A female patient, about 75 years old · this is a dermoscopic photograph of a skin lesion: 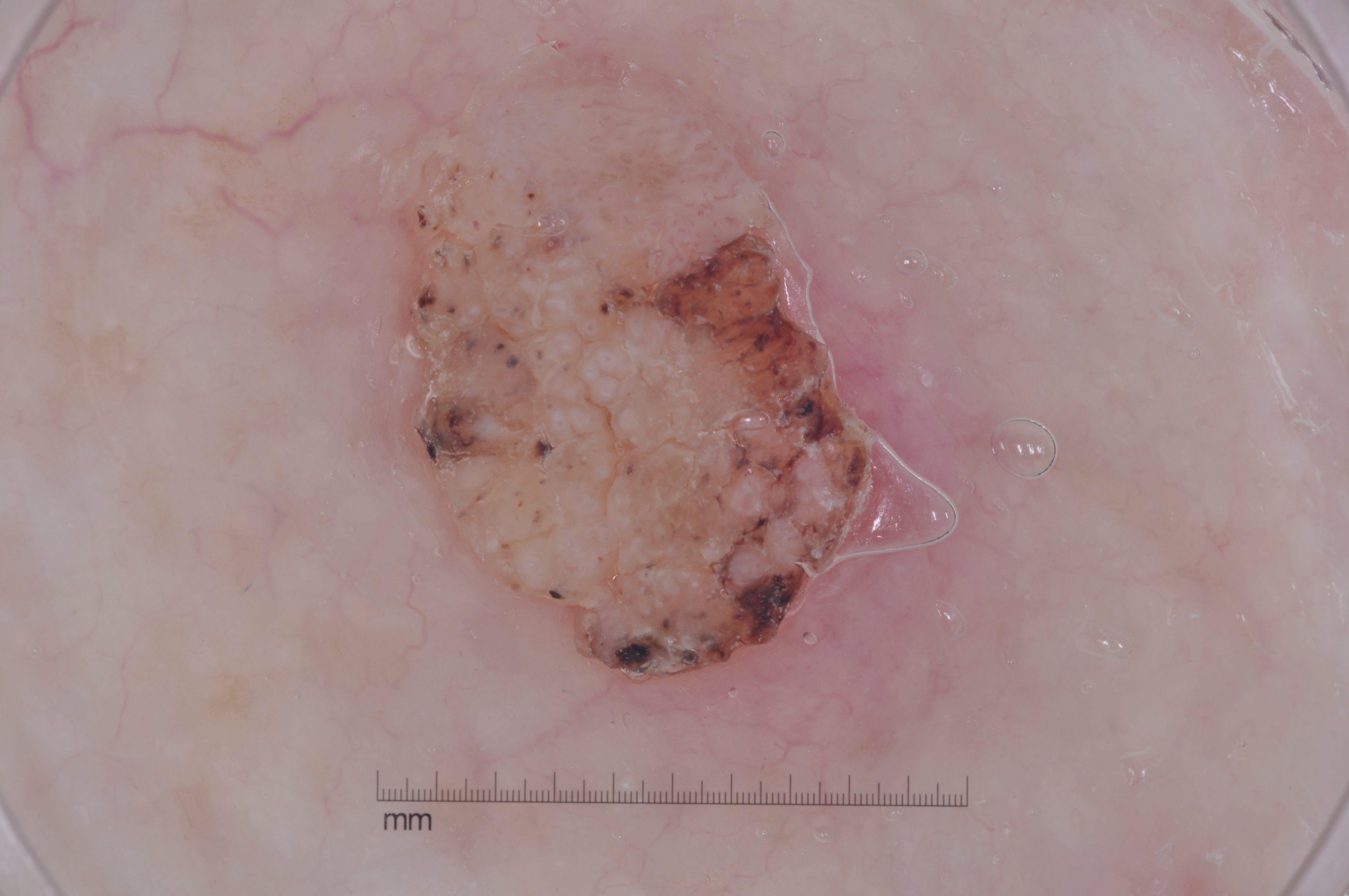dermoscopic features: milia-like cysts; lesion bbox: x1=285 y1=14 x2=1022 y2=777; size: large; assessment: a seborrheic keratosis.